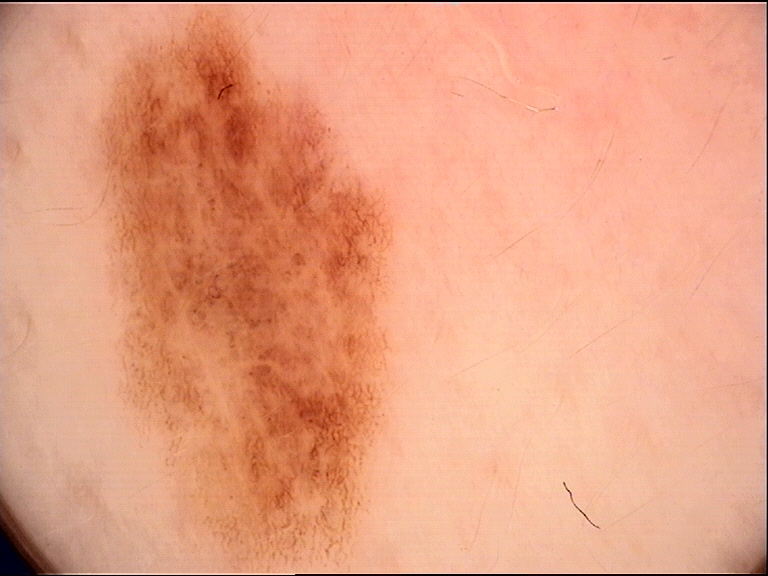Case:
- image type — dermatoscopy
- class — dysplastic junctional nevus (expert consensus)